The photograph is a close-up of the affected area · skin tone: Fitzpatrick phototype I; non-clinician graders estimated MST 2:
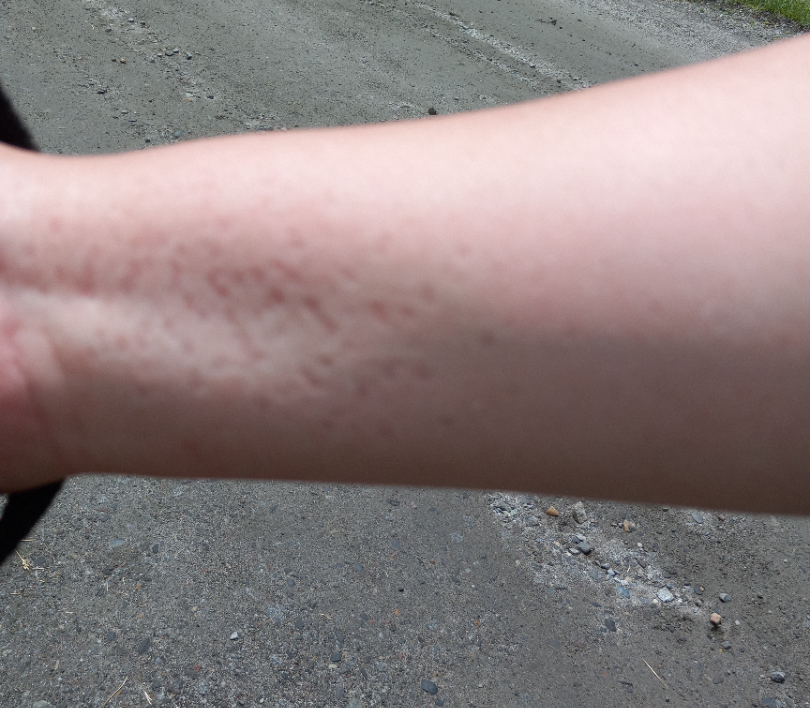assessment — could not be assessed